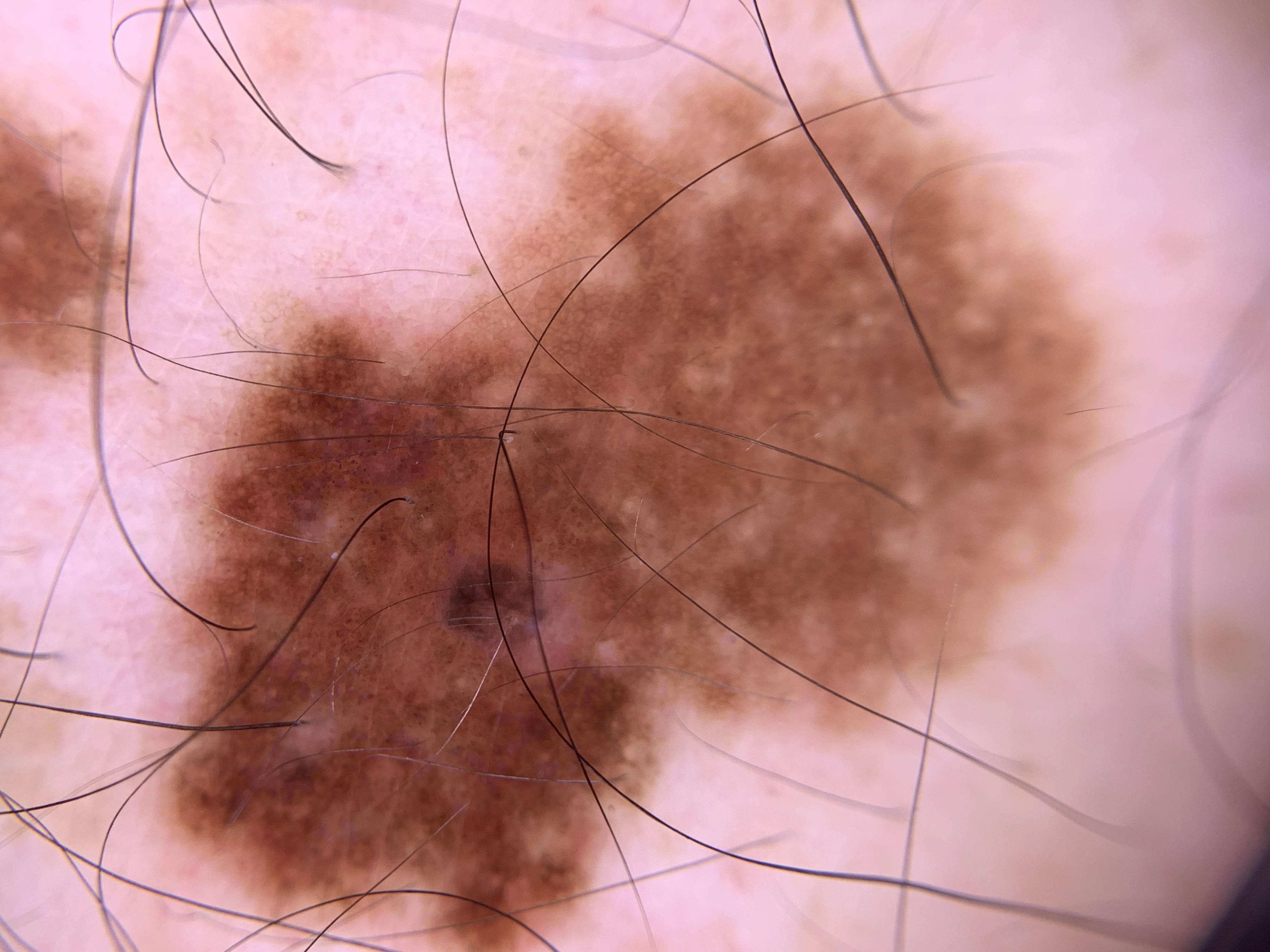patient = male, aged around 45
image = contact-polarized dermoscopy
location = the trunk
pathology = Nevus (biopsy-proven)